A patient age 25 — 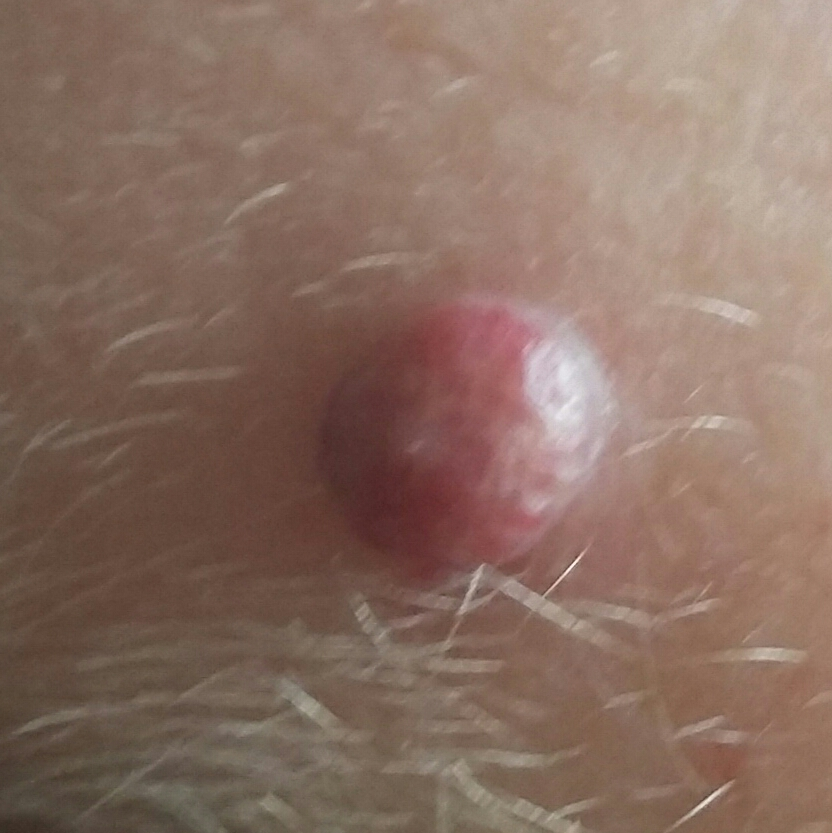The diagnostic impression was a nevus.